The patient says their skin tans without first burning; a female patient age 78; the patient describes having numerous moles; acquired for a research image collection, with no referral diagnosis — 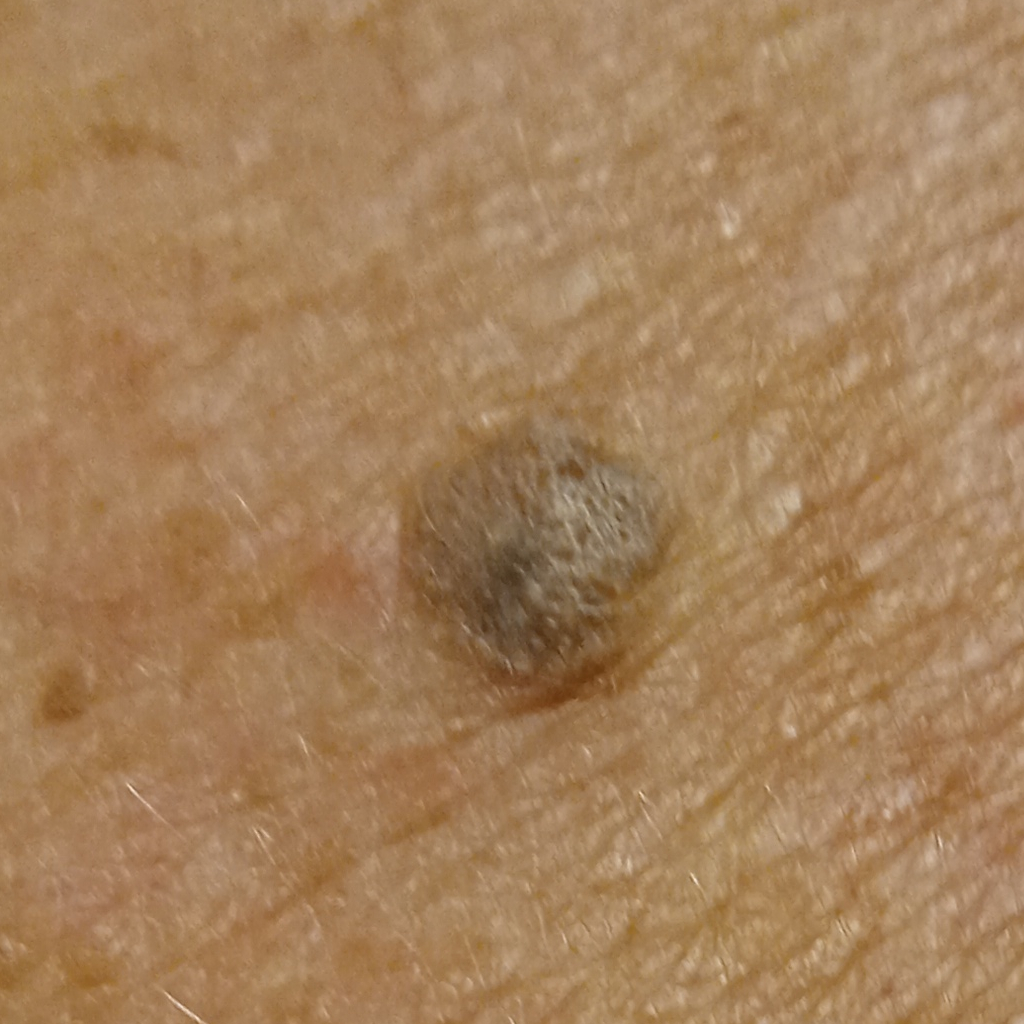<record>
  <lesion_location>the back</lesion_location>
  <diagnosis>
    <name>seborrheic keratosis</name>
    <malignancy>benign</malignancy>
  </diagnosis>
</record>